Imaged for a research study, with no referral diagnosis recorded; a female patient 84 years of age; a clinical close-up of a skin lesion:
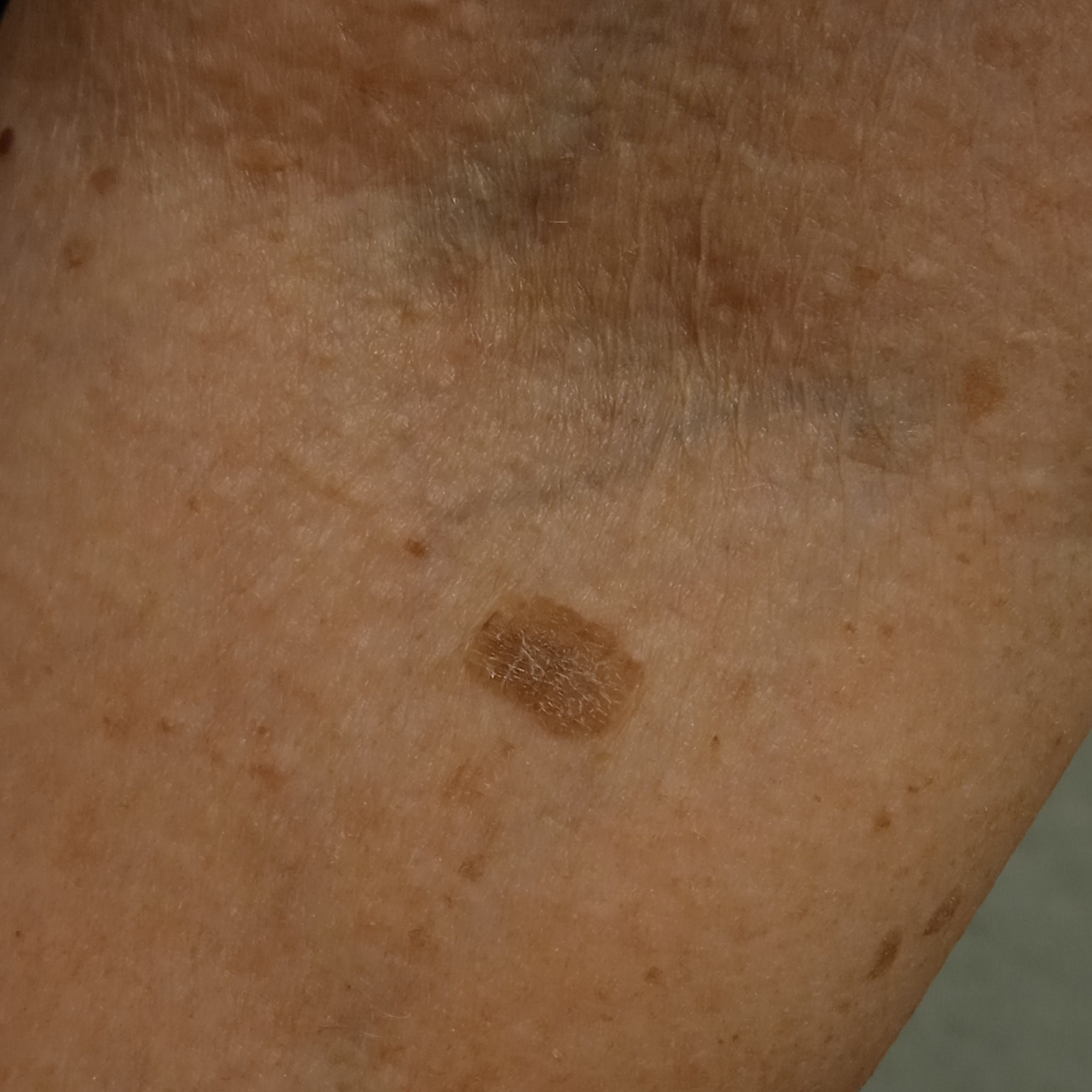Findings:
- body site · an arm
- size · 11.2 mm
- diagnostic label · seborrheic keratosis (dermatologist consensus)